A dermoscopic close-up of a skin lesion.
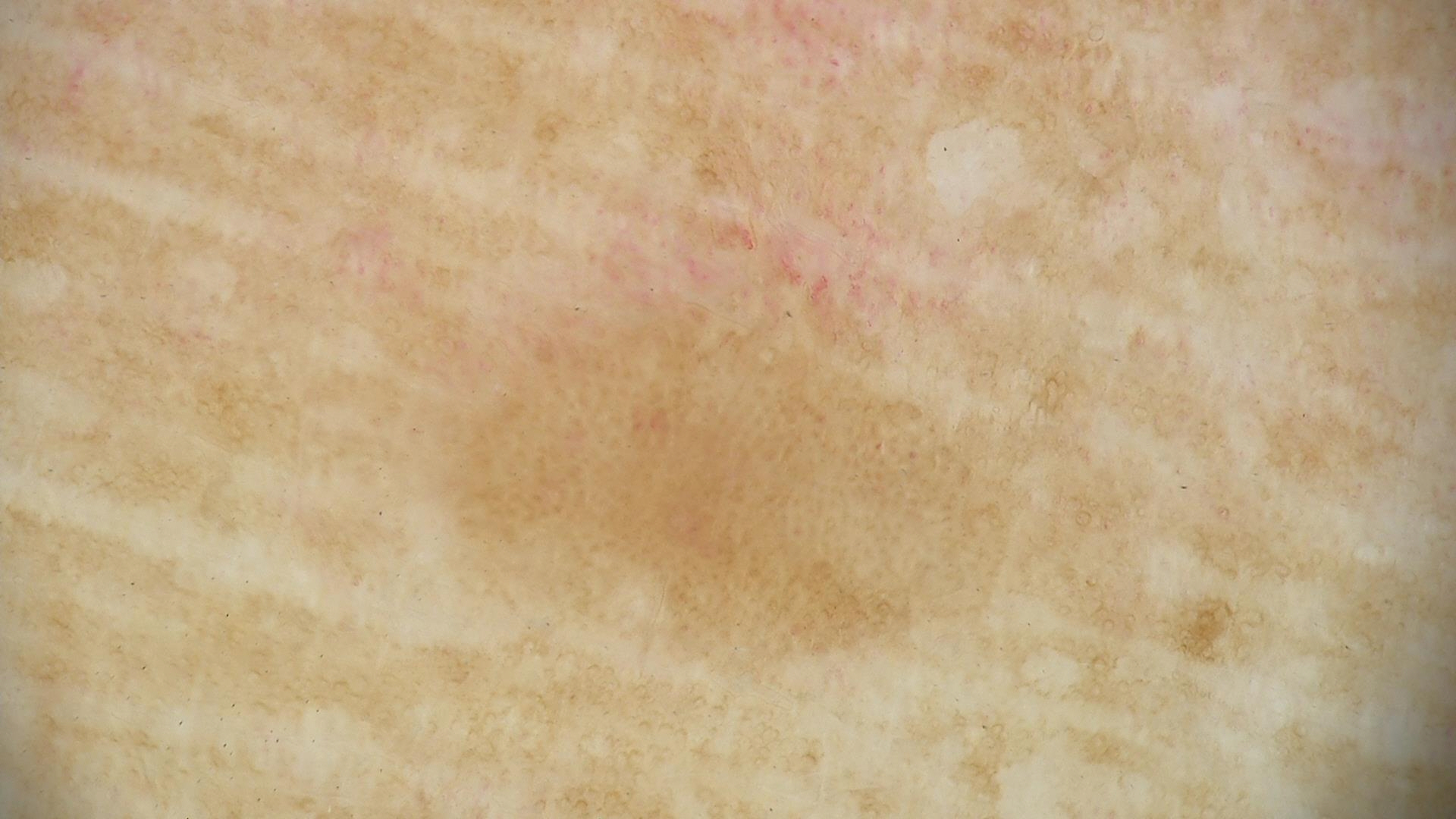Diagnosed as a benign, keratinocytic lesion — a seborrheic keratosis.